A clinical close-up photograph of a skin lesion; the chart notes alcohol use, tobacco use, no prior skin cancer (patient or family), and no prior malignancy (patient or family); the patient was assessed as FST II; a male subject in their late 50s: 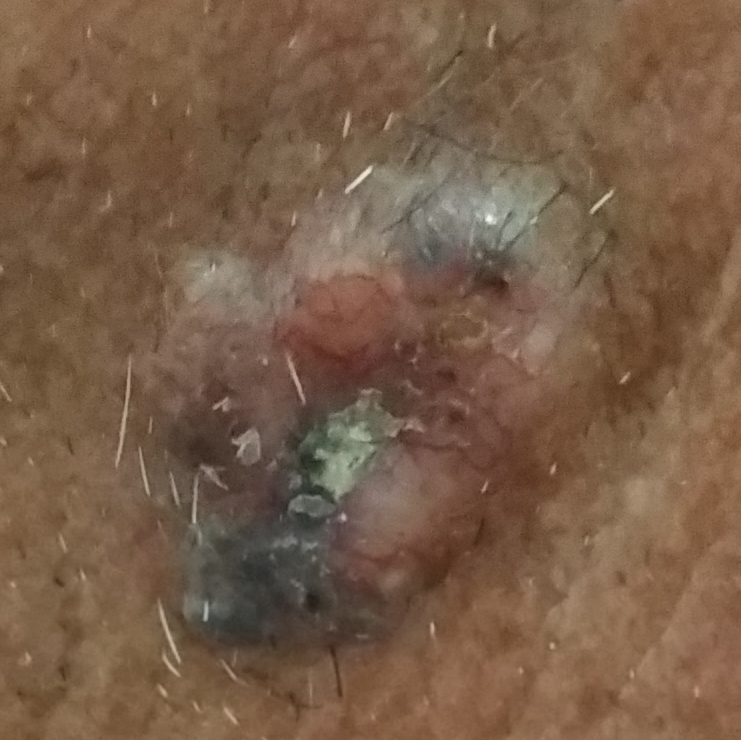Q: What are the lesion's dimensions?
A: approx. 20 × 15 mm
Q: What symptoms does the patient report?
A: pain, bleeding, growth, elevation, itching
Q: What did the workup show?
A: basal cell carcinoma (biopsy-proven)